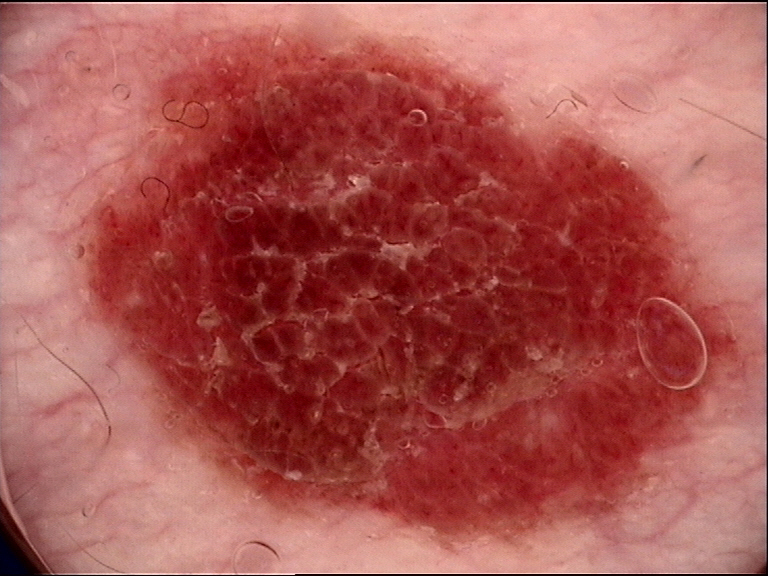A dermatoscopic image of a skin lesion. Diagnosed as a banal lesion — a compound nevus.